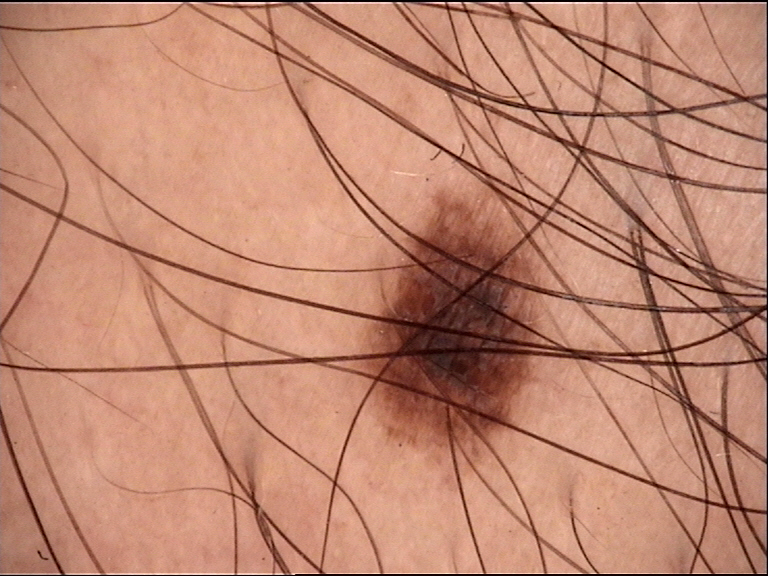Findings:
A dermoscopic close-up of a skin lesion.
Conclusion:
Consistent with a dysplastic junctional nevus.